The patient is a male aged 40–49; the affected area is the arm, front of the torso and leg; the photograph was taken at an angle.
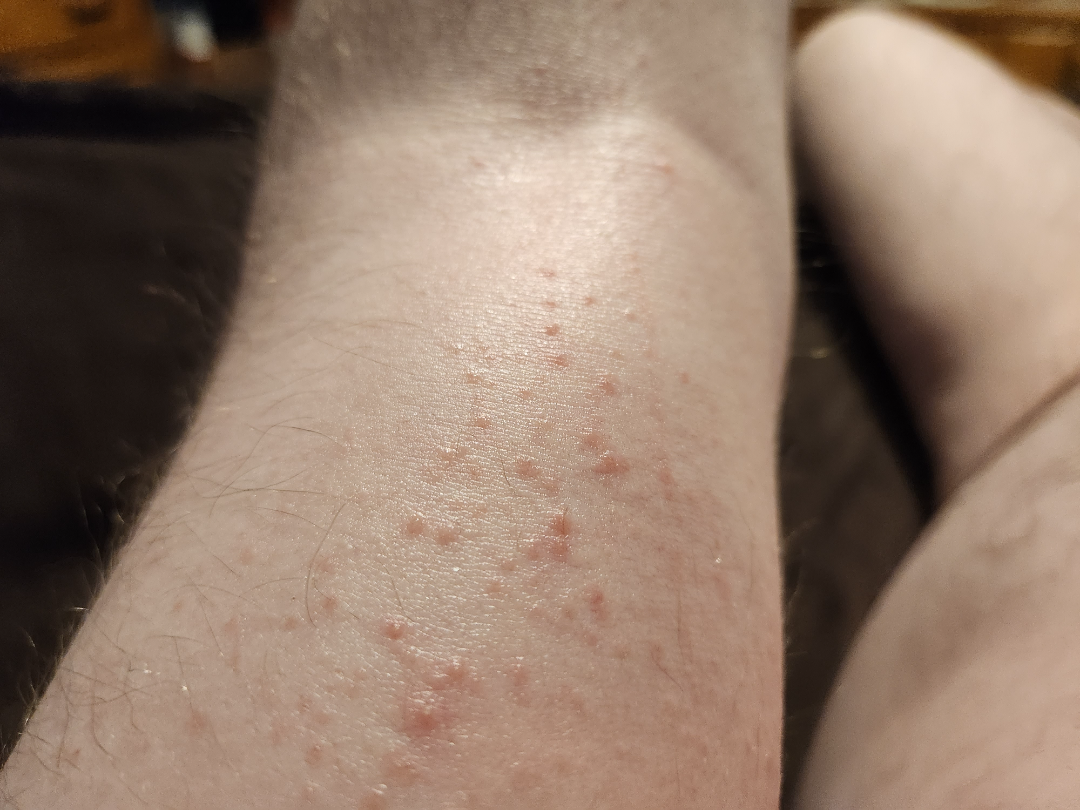* history — less than one week
* surface texture — raised or bumpy
* dermatologist impression — the favored diagnosis is Eczema; with consideration of Irritant Contact Dermatitis; also on the differential is Allergic Contact Dermatitis; less likely is Folliculitis